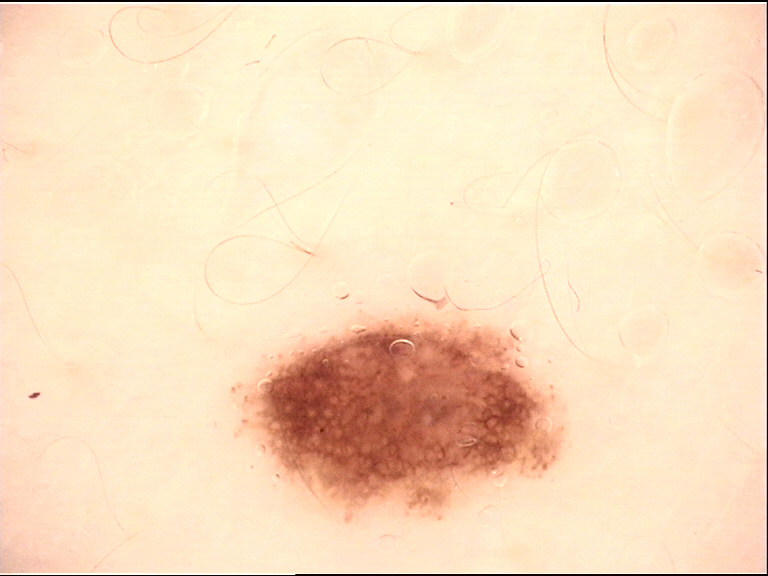<dermoscopy>
  <image>dermoscopy</image>
  <diagnosis>
    <name>dysplastic junctional nevus</name>
    <code>jd</code>
    <malignancy>benign</malignancy>
    <super_class>melanocytic</super_class>
    <confirmation>expert consensus</confirmation>
  </diagnosis>
</dermoscopy>